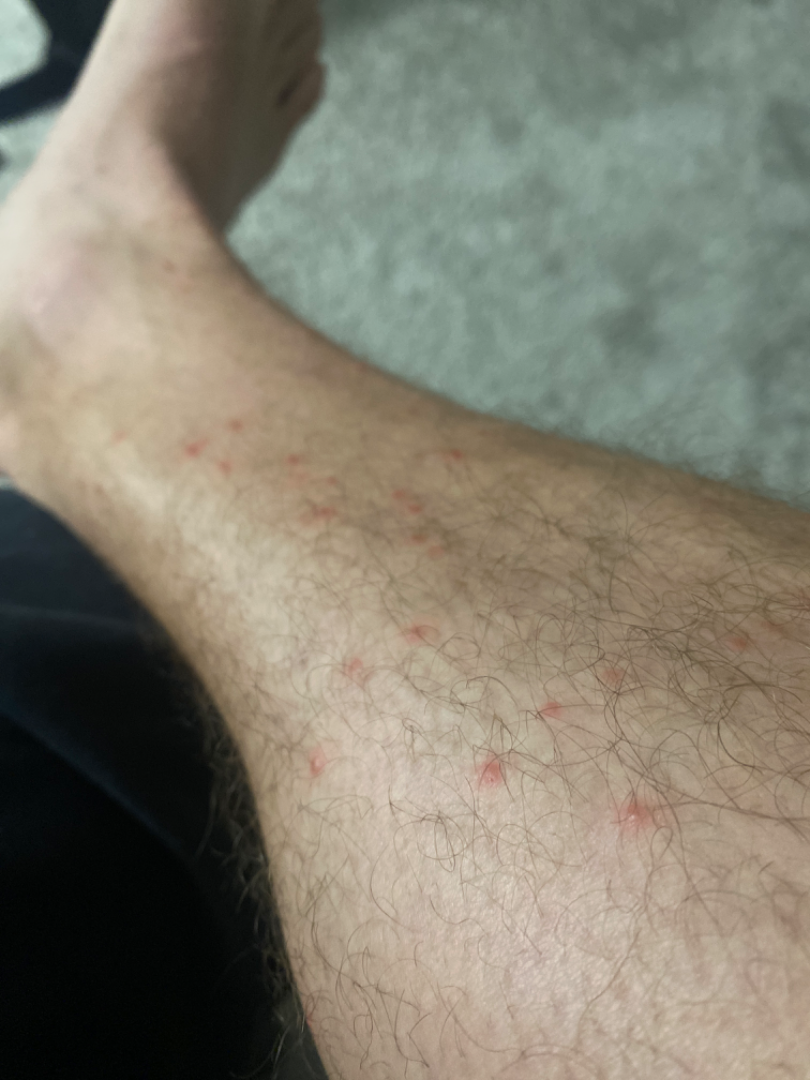The leg and top or side of the foot are involved. An image taken at an angle. Male subject, age 30–39. The reviewing clinician's impression was: Lichen planus/lichenoid eruption (possible); Insect Bite (possible); Eczema (lower probability).